A male patient in their 70s:
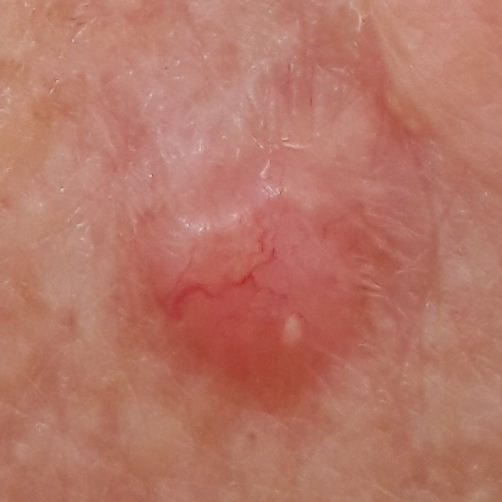body site: the nose; reported symptoms: itching, growth, elevation, bleeding; diagnostic label: basal cell carcinoma (biopsy-proven).